A dermoscopic close-up of a skin lesion:
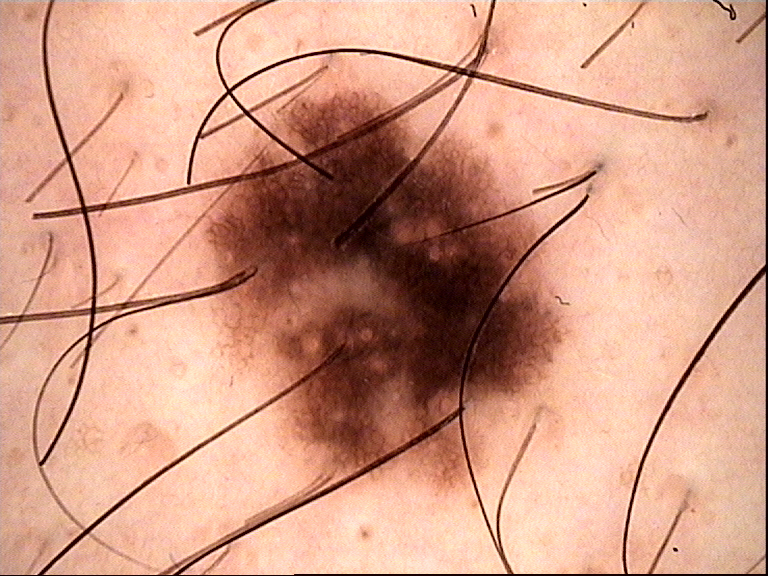diagnosis=dysplastic junctional nevus (expert consensus).